A female patient roughly 85 years of age or older. Recorded as FST II.
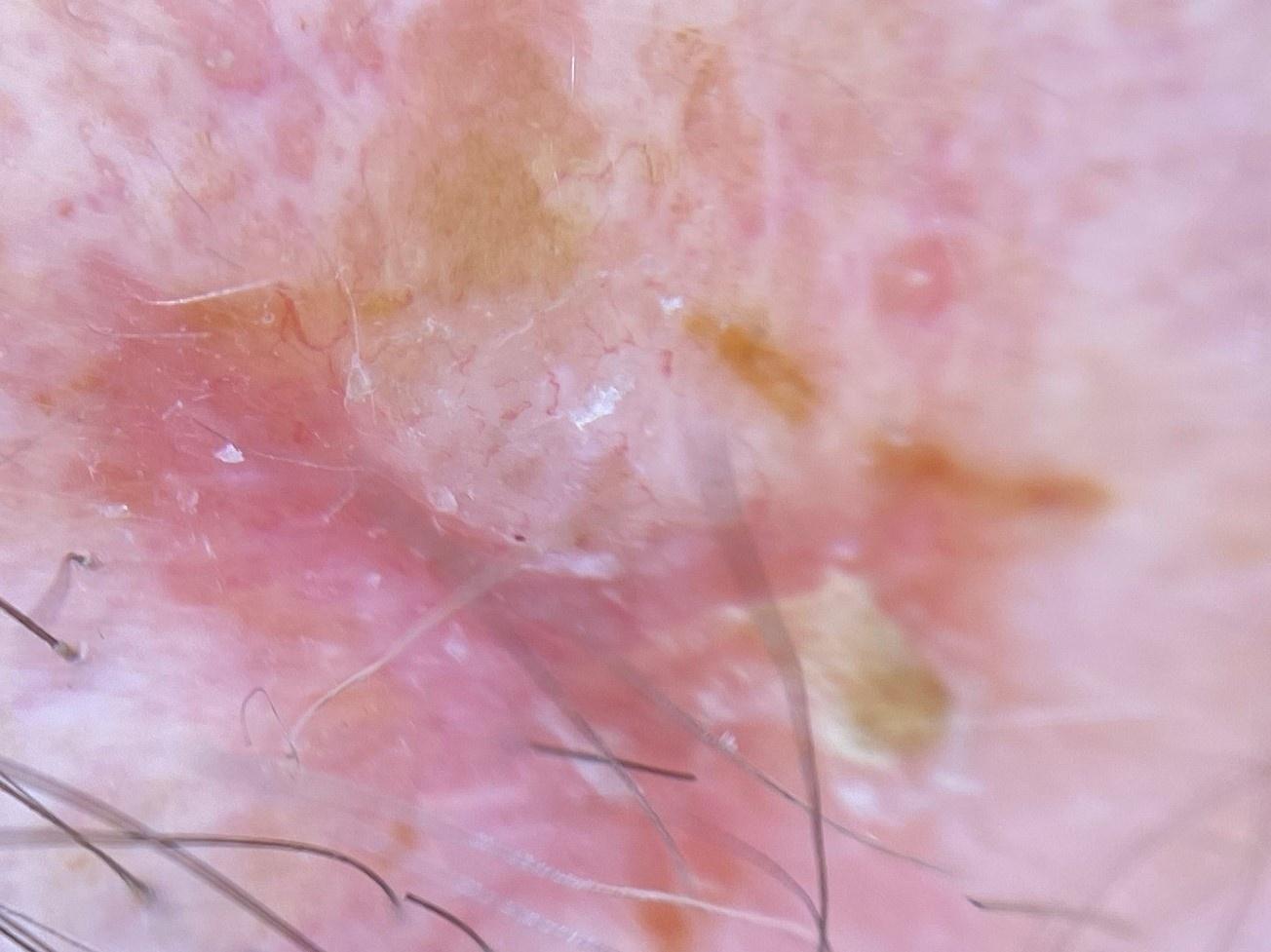Notes:
• body site: the head or neck
• diagnostic label: Basal cell carcinoma (biopsy-proven)